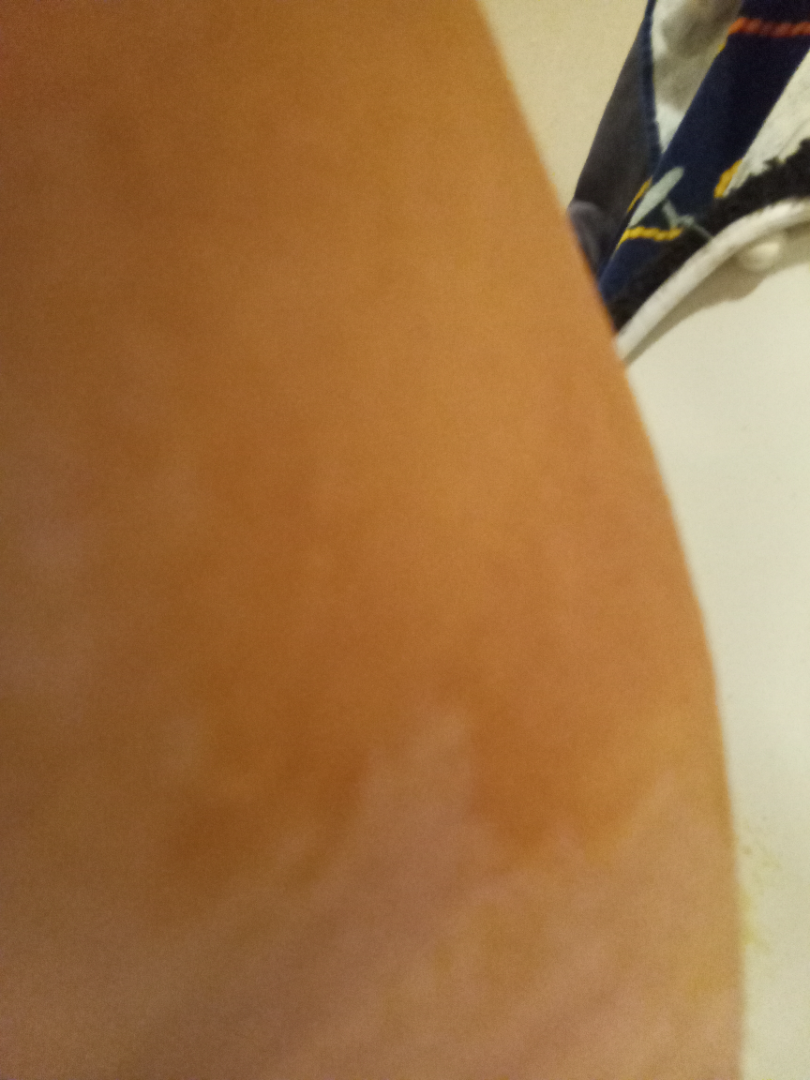assessment — ungradable on photographic review